A dermoscopic close-up of a skin lesion.
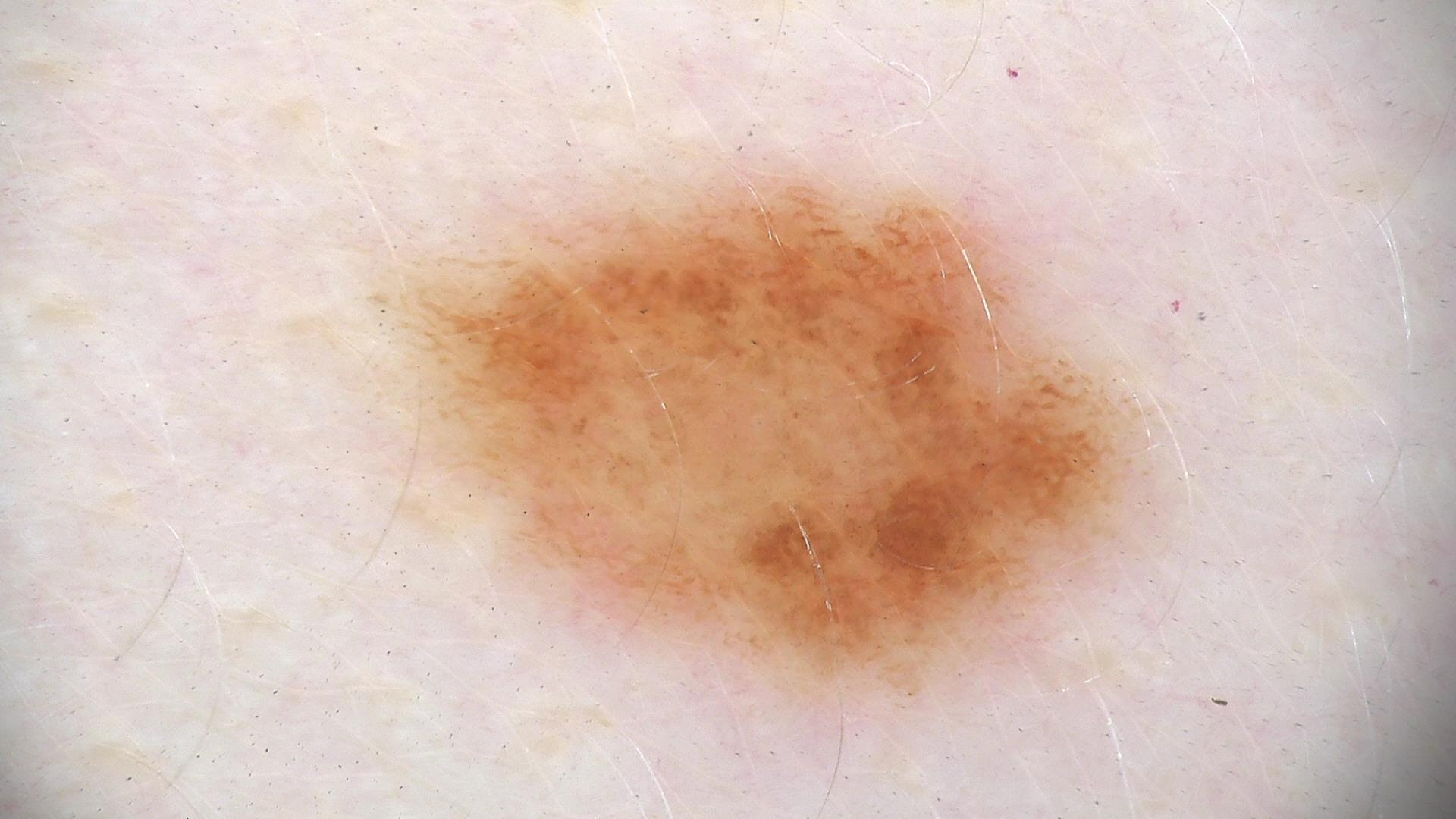label=dysplastic junctional nevus (expert consensus).